The patient describes having few moles overall; the patient says their skin reddens with sun exposure; a female patient age 39: 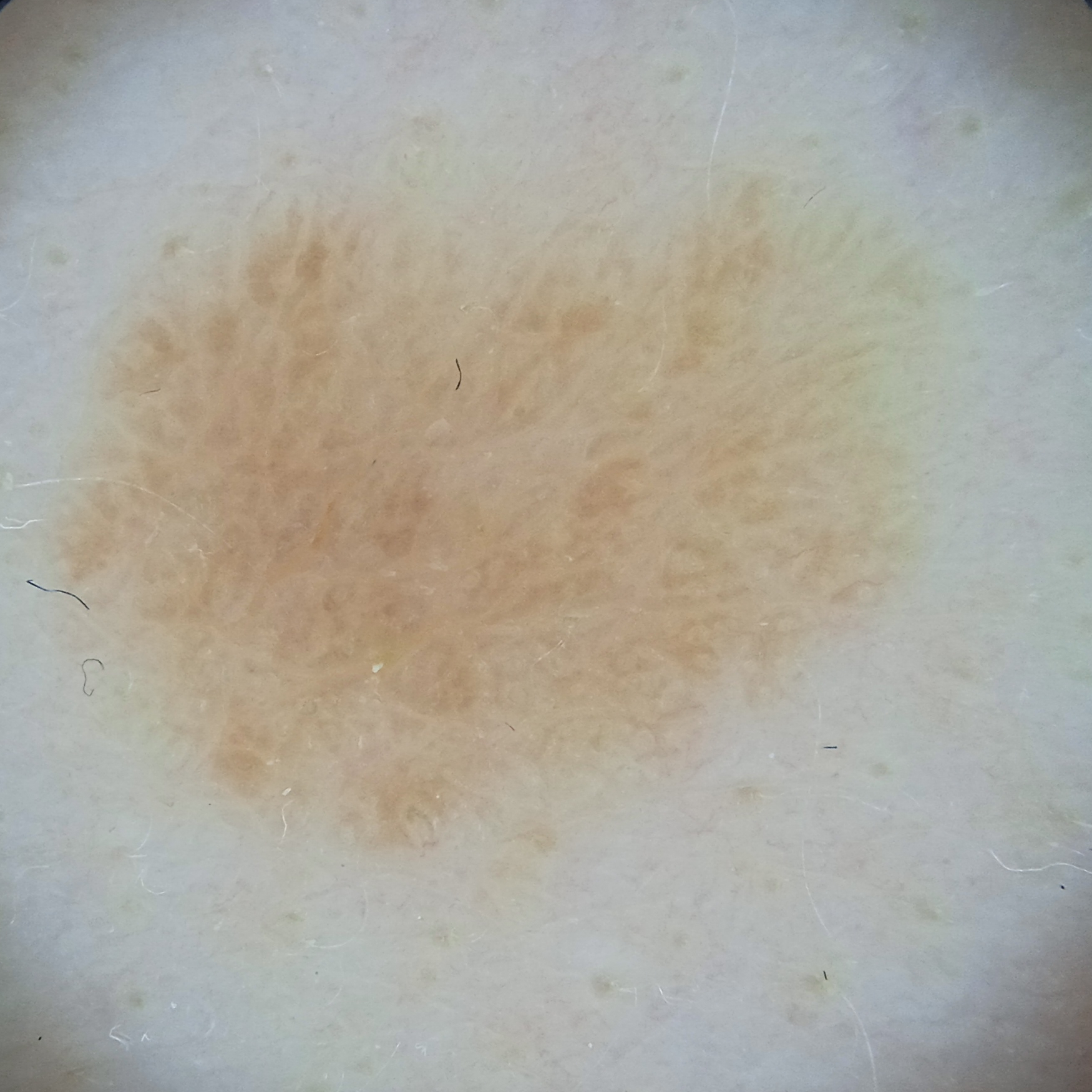Summary: The lesion measures approximately 10.1 mm. Conclusion: The diagnostic impression was a seborrheic keratosis.